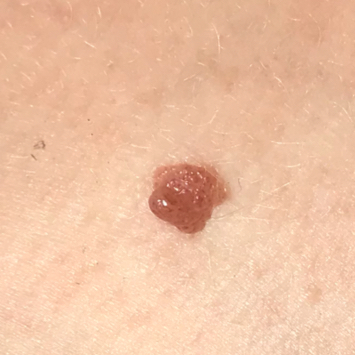Expert review favored a nevus.